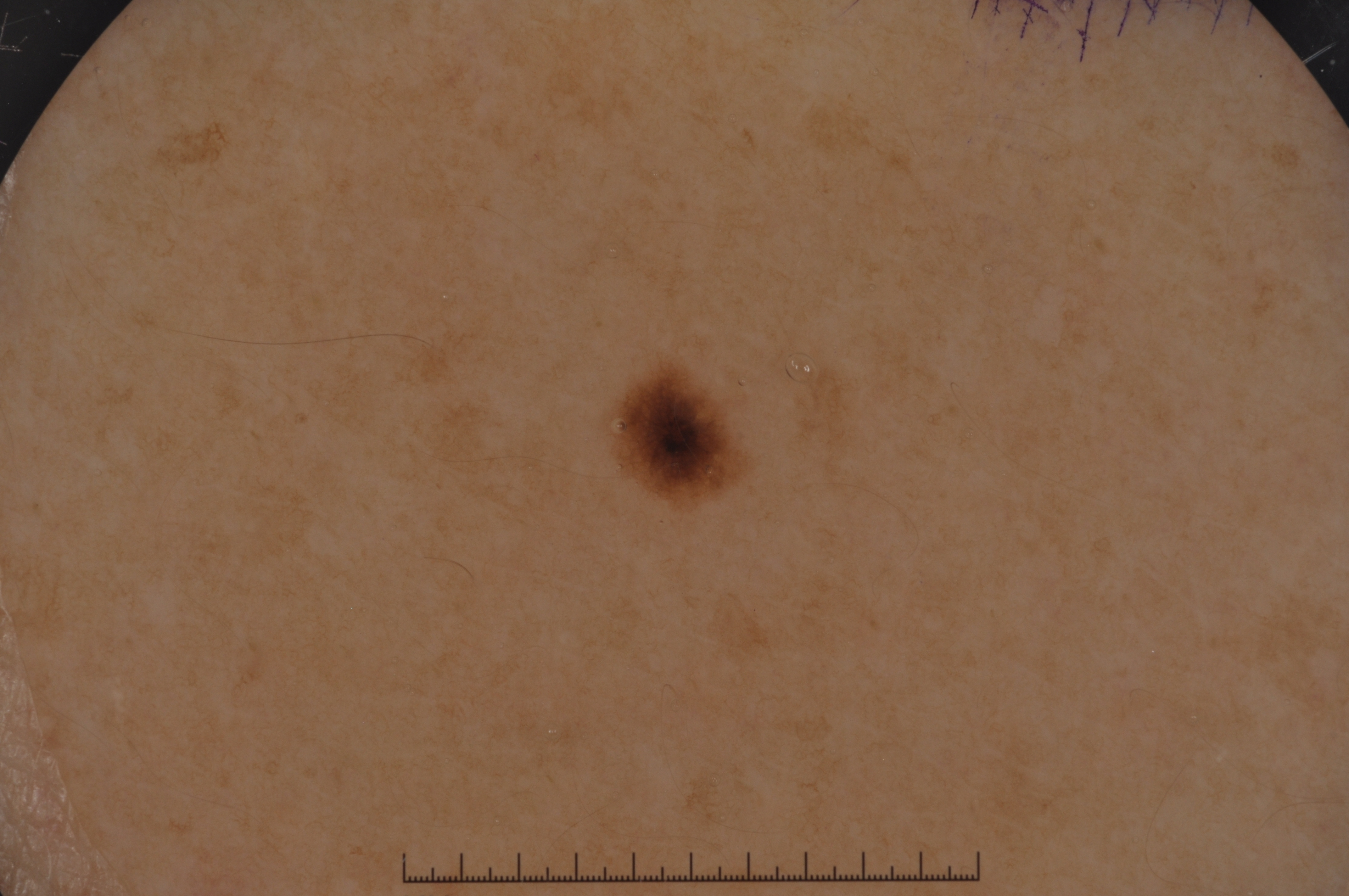  image:
    modality: dermoscopy
  lesion_location:
    bbox_xyxy:
      - 622
      - 378
      - 738
      - 497
  diagnosis:
    name: melanocytic nevus
    malignancy: benign
    lineage: melanocytic
    provenance: clinical